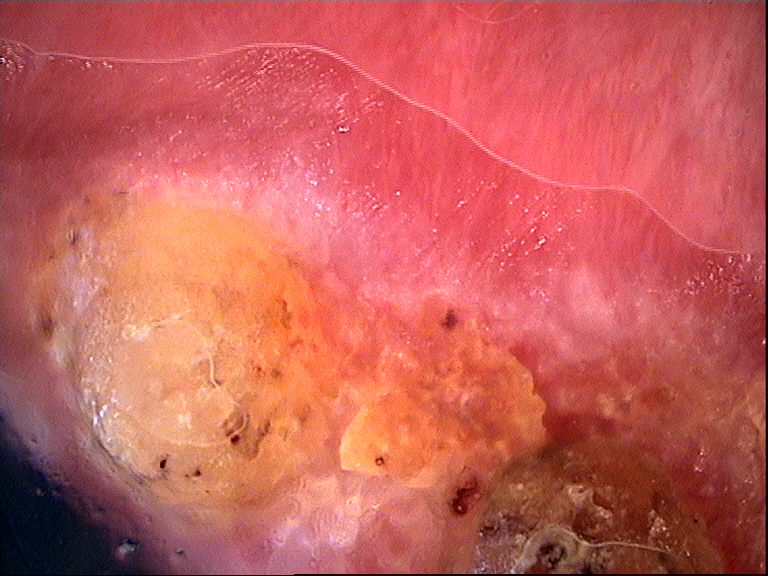Q: What kind of image is this?
A: dermoscopy
Q: What is the lesion category?
A: keratinocytic
Q: What is this lesion?
A: squamous cell carcinoma (biopsy-proven)